No relevant systemic symptoms. The patient described the issue as a rash. This is a close-up image. Reported lesion symptoms include pain, itching and burning. Reported duration is less than one week. Located on the front of the torso. The contributor is a female aged 50–59 — 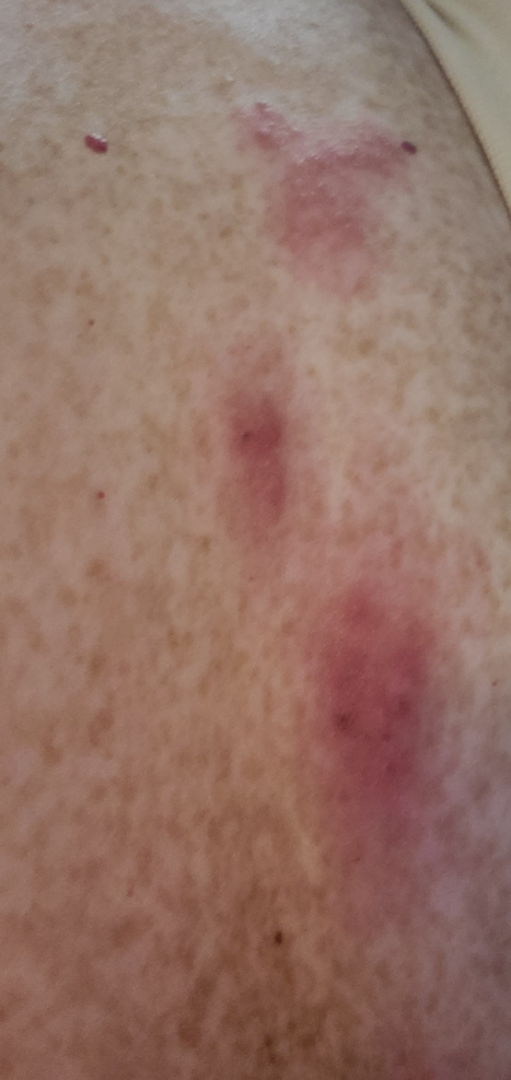The case was indeterminate on photographic review.